A dermoscopy image of a single skin lesion — 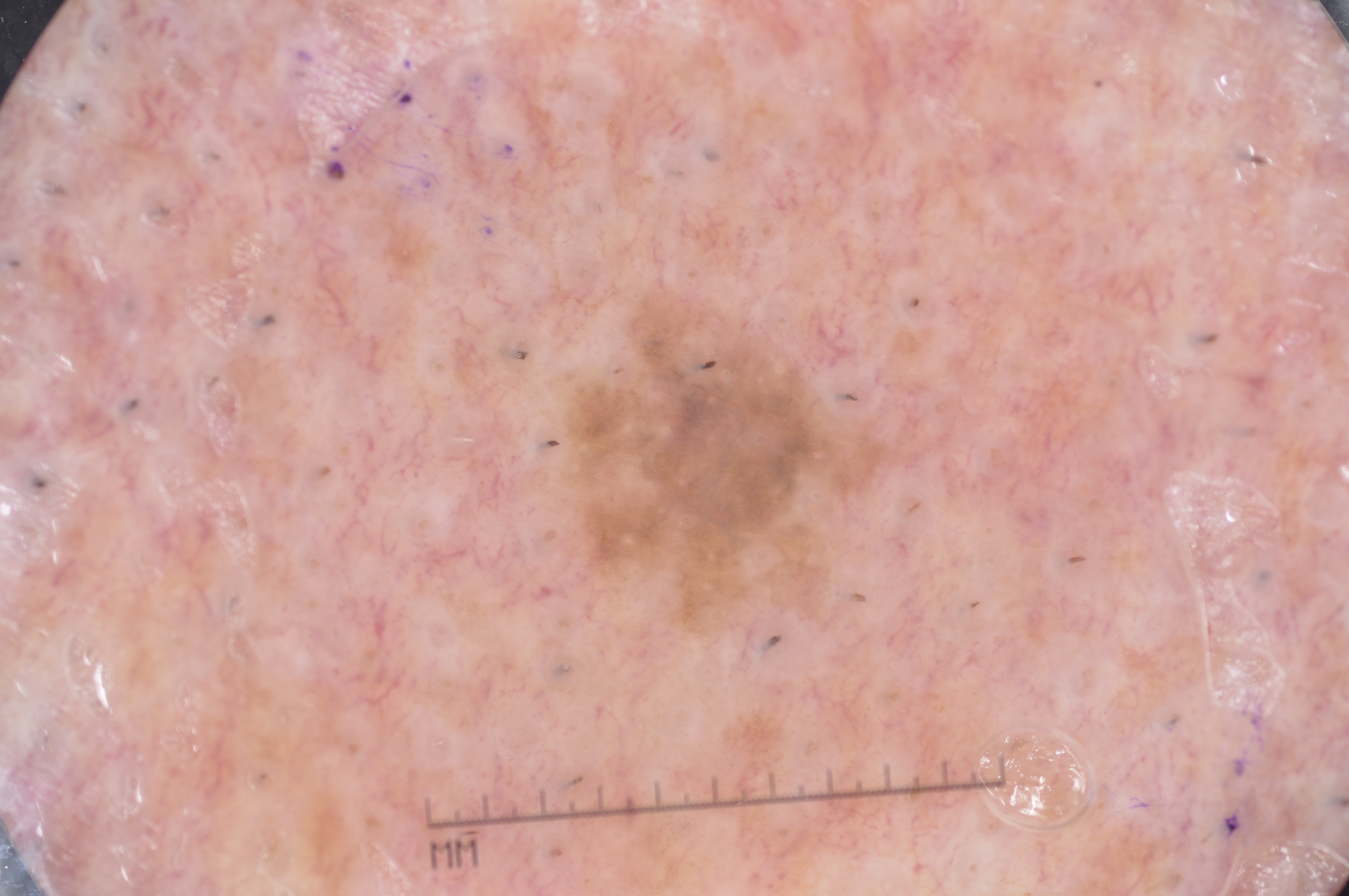{
  "lesion_location": {
    "bbox_xyxy": [
      569,
      315,
      875,
      602
    ]
  },
  "diagnosis": {
    "name": "melanoma",
    "malignancy": "malignant",
    "lineage": "melanocytic",
    "provenance": "histopathology"
  }
}